The lesion involves the head or neck. The patient described the issue as a rash. The photo was captured at an angle. Texture is reported as raised or bumpy — 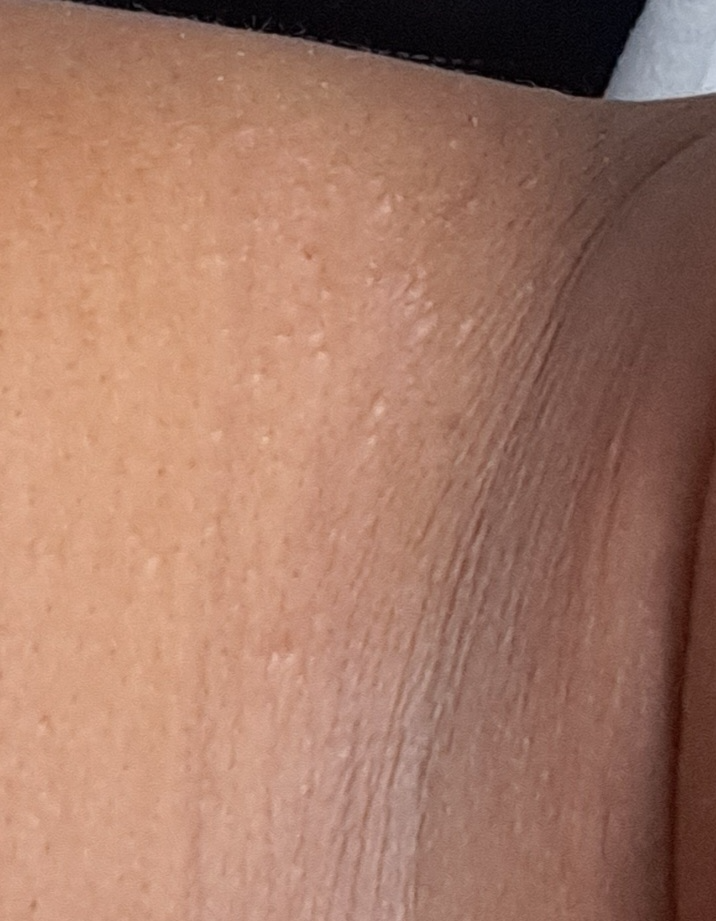Assessment: The case was indeterminate on photographic review.